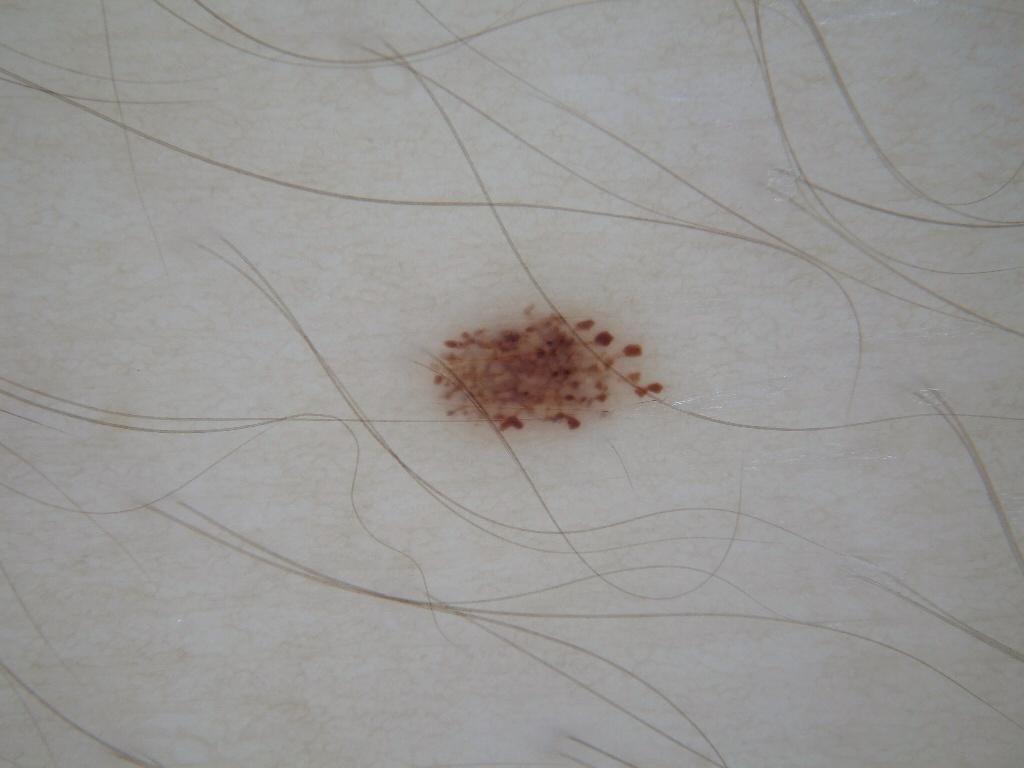Case summary: A female patient, aged around 30. A dermoscopic image of a skin lesion. On dermoscopy, the lesion shows pigment network. The lesion is small relative to the field of view. With coordinates (x1, y1, x2, y2), the lesion is located at bbox=[420, 295, 677, 441]. Impression: The lesion was assessed as a melanocytic nevus, a benign skin lesion.